Close-up view: 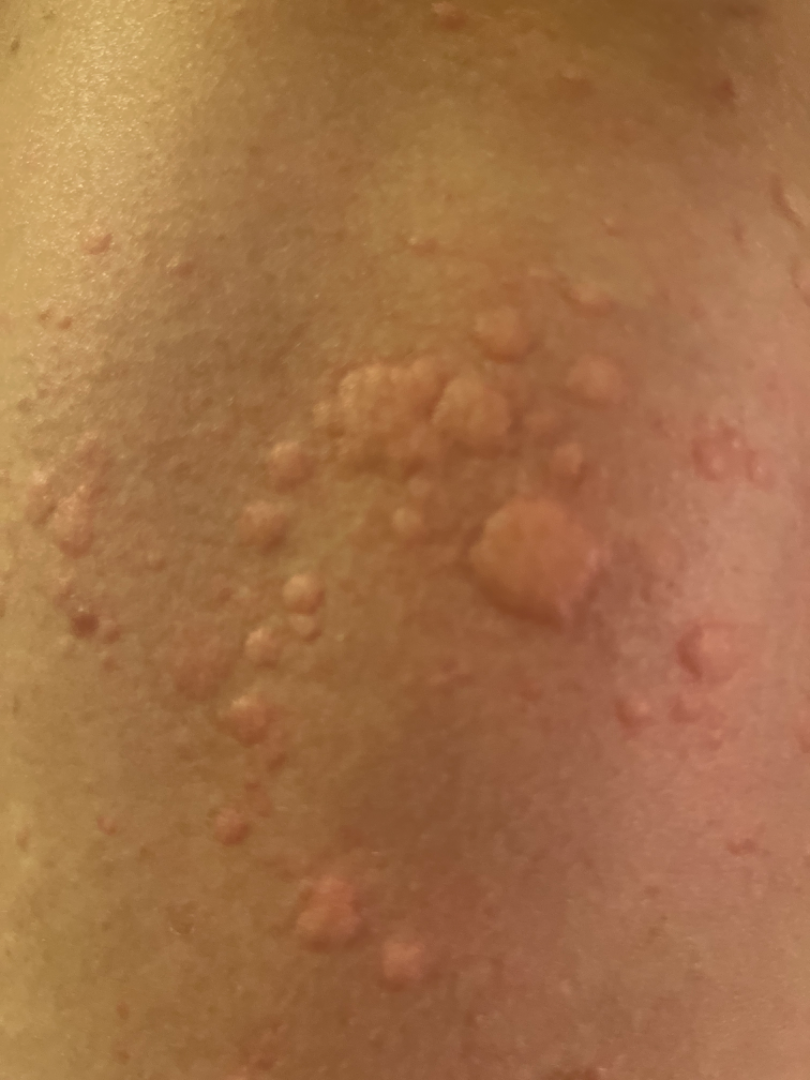differential:
  leading:
    - Urticaria